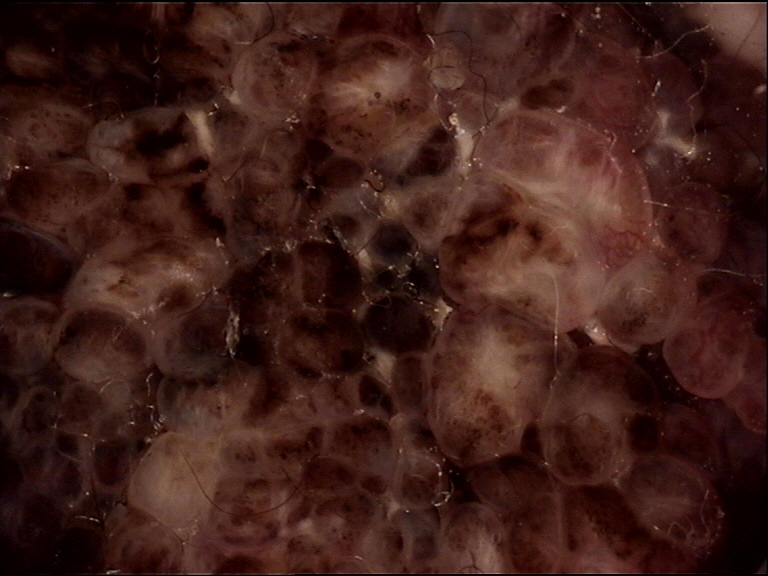A dermoscopic image of a skin lesion.
This is a banal lesion.
Labeled as a congenital compound nevus.